A clinical photo of a skin lesion taken with a smartphone. The chart notes prior skin cancer (patient or family), alcohol use, prior malignancy (patient or family), pesticide exposure, and no tobacco use. The patient was assessed as Fitzpatrick II. A male subject 33 years of age.
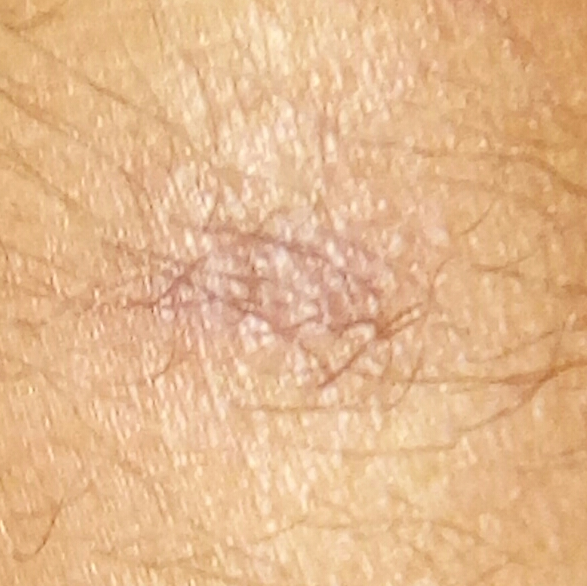The lesion was found on an arm. The lesion measures 11 × 10 mm. Histopathologically confirmed as an actinic keratosis.